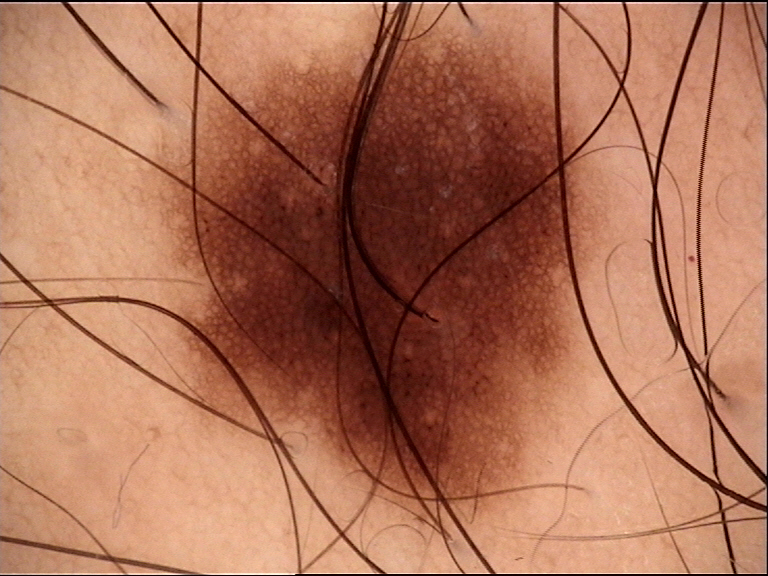Labeled as a junctional nevus.